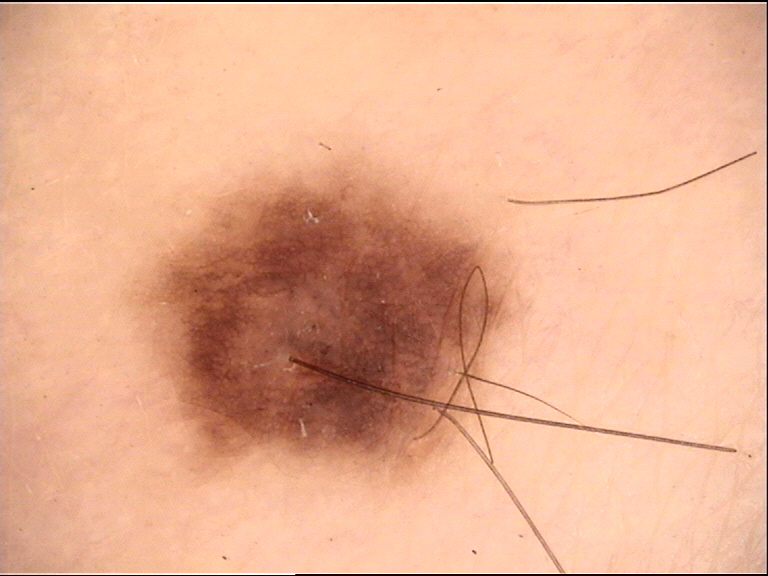| feature | finding |
|---|---|
| label | compound nevus (expert consensus) |